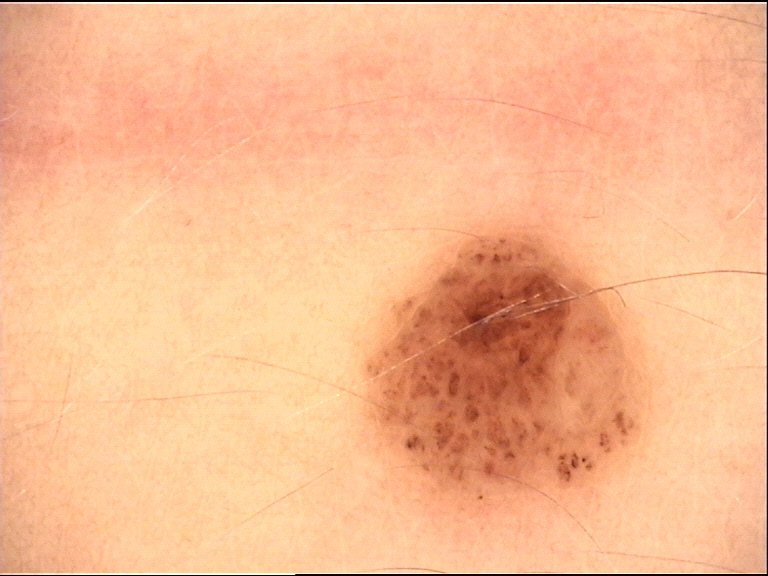{
  "image": "dermatoscopy",
  "diagnosis": {
    "name": "compound nevus",
    "code": "cb",
    "malignancy": "benign",
    "super_class": "melanocytic",
    "confirmation": "expert consensus"
  }
}